This is a close-up image.
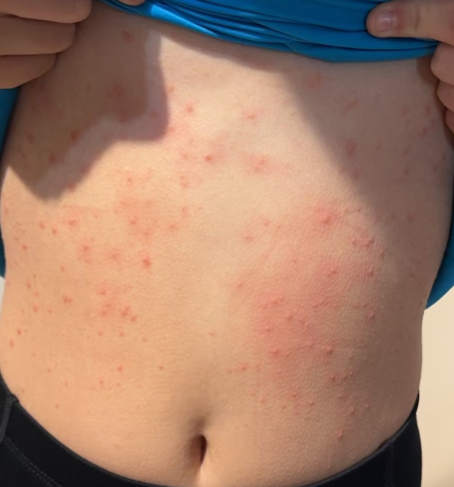The dermatologist could not determine a likely condition from the photograph alone.
Skin tone: Fitzpatrick skin type II.